A dermatoscopic image of a skin lesion.
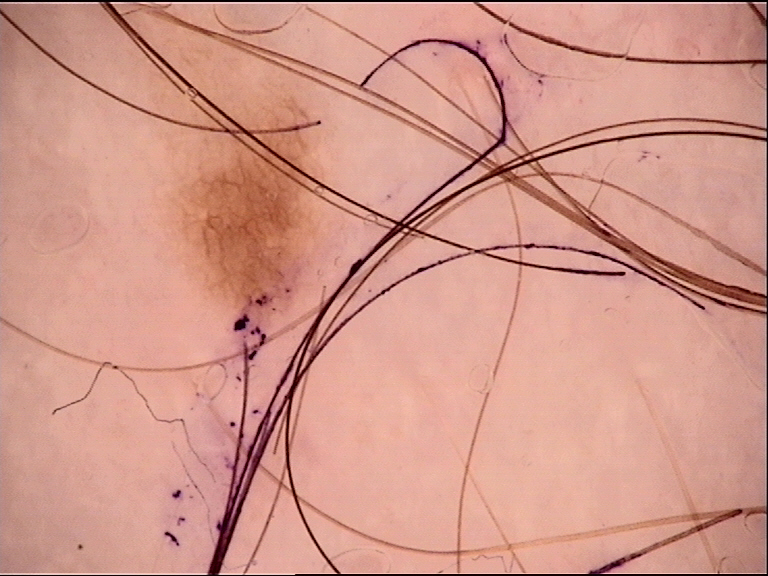Q: What is this lesion?
A: junctional nevus (expert consensus)